A female patient age 66. History notes alcohol use, prior skin cancer (patient or family), prior malignancy (patient or family), and no tobacco use. The patient is Fitzpatrick phototype II. A clinical photo of a skin lesion taken with a smartphone.
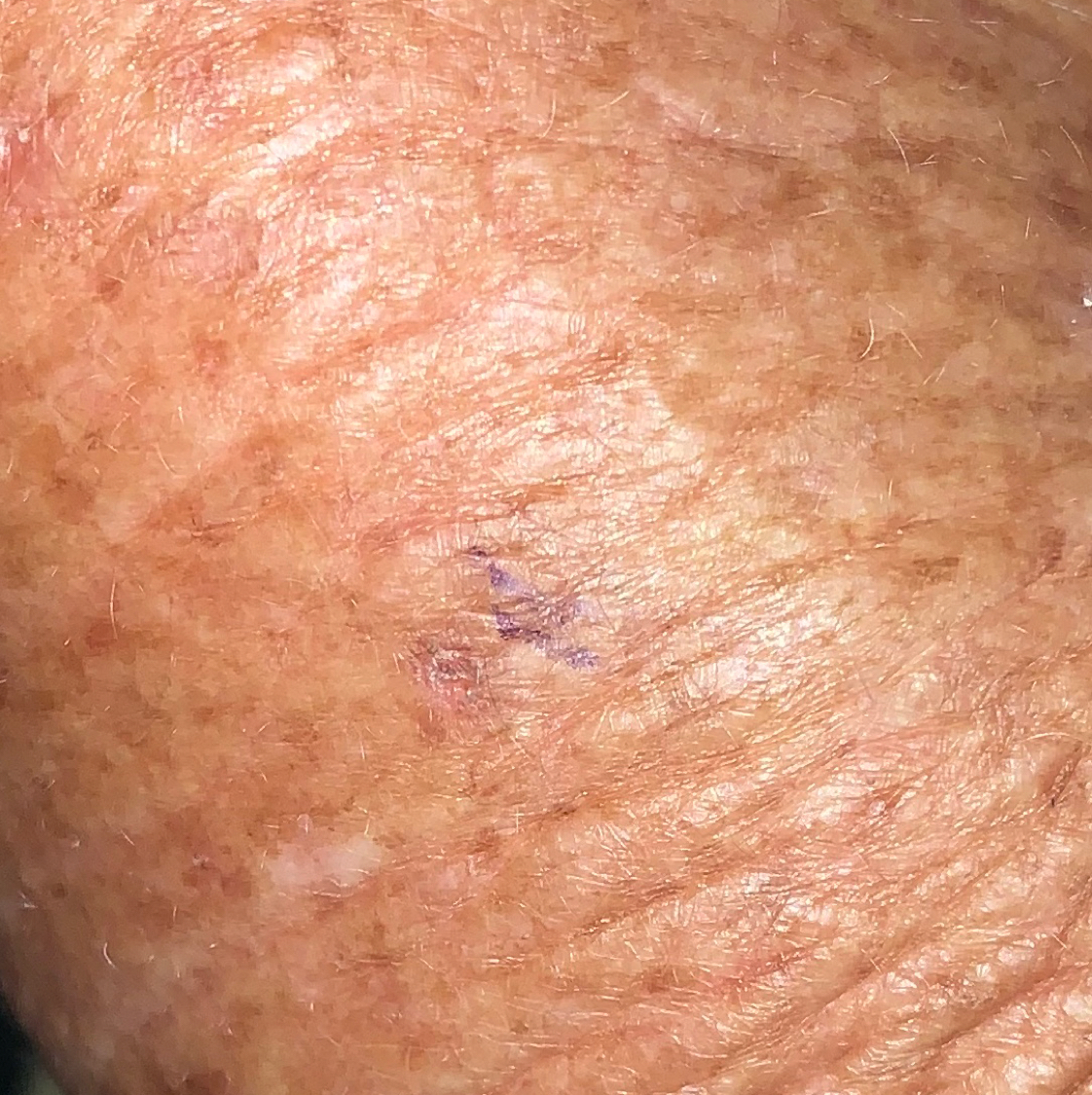patient-reported symptoms = elevation | impression = actinic keratosis (clinical consensus).